A female patient aged 61; the chart records prior malignancy (patient or family) and no prior skin cancer (patient or family); a clinical photo of a skin lesion taken with a smartphone: 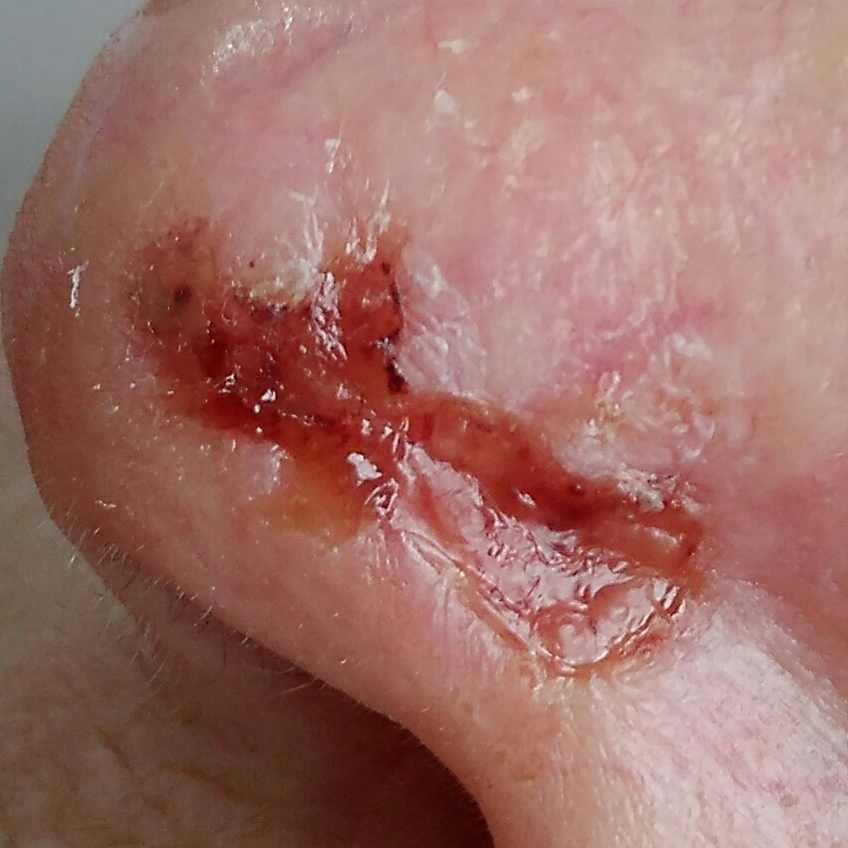The lesion is roughly 15 by 7 mm. By the patient's account, the lesion has grown, is elevated, has bled, itches, and hurts. Histopathological examination showed a basal cell carcinoma.